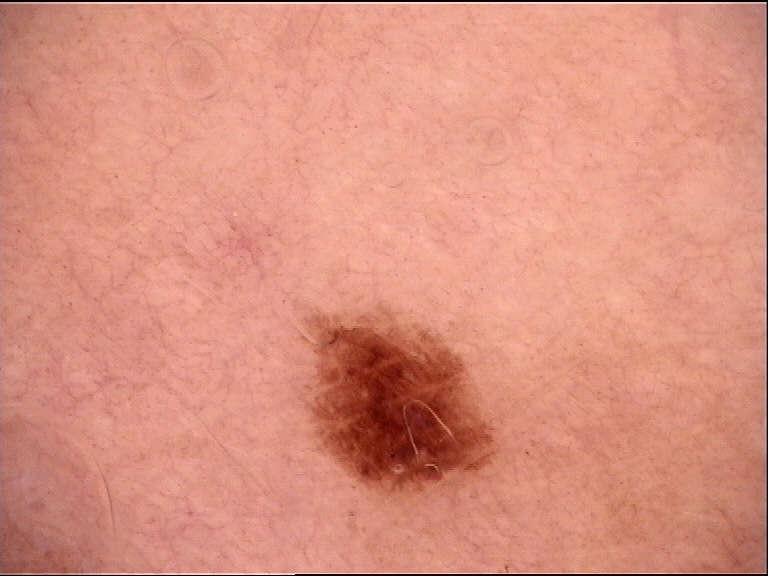| field | value |
|---|---|
| subtype | banal |
| assessment | junctional nevus (expert consensus) |